The photograph was taken at an angle; the lesion involves the top or side of the foot — 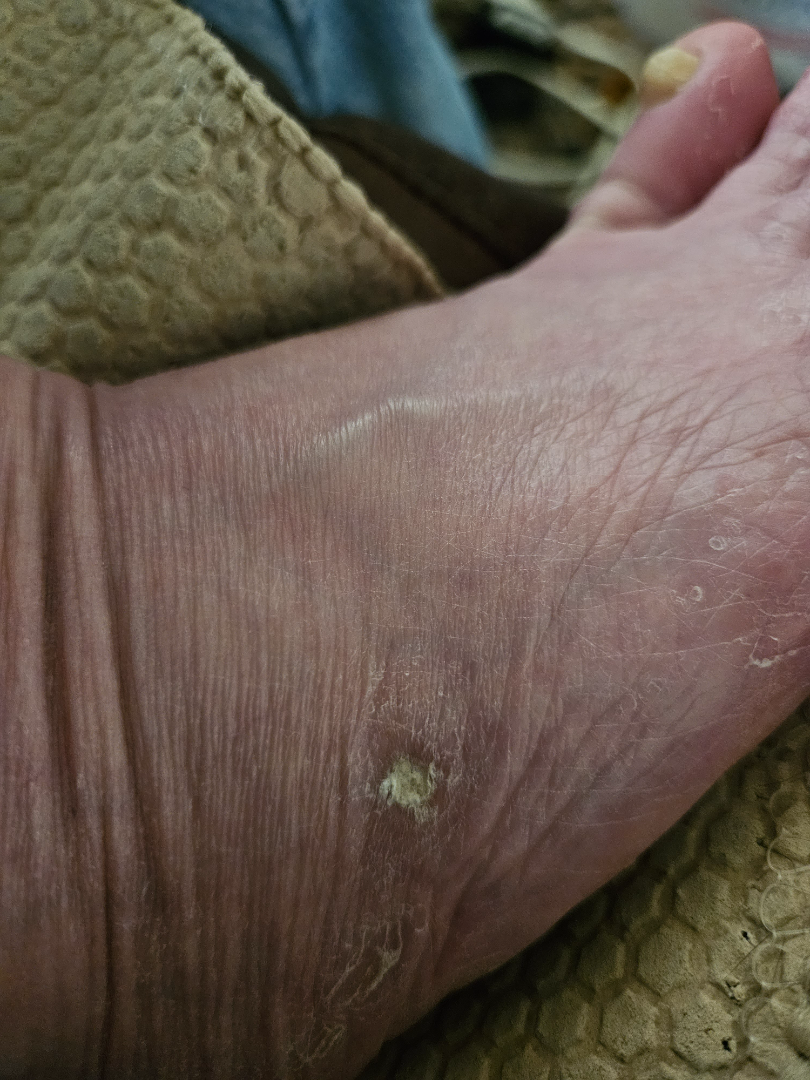{
  "assessment": "not assessable"
}